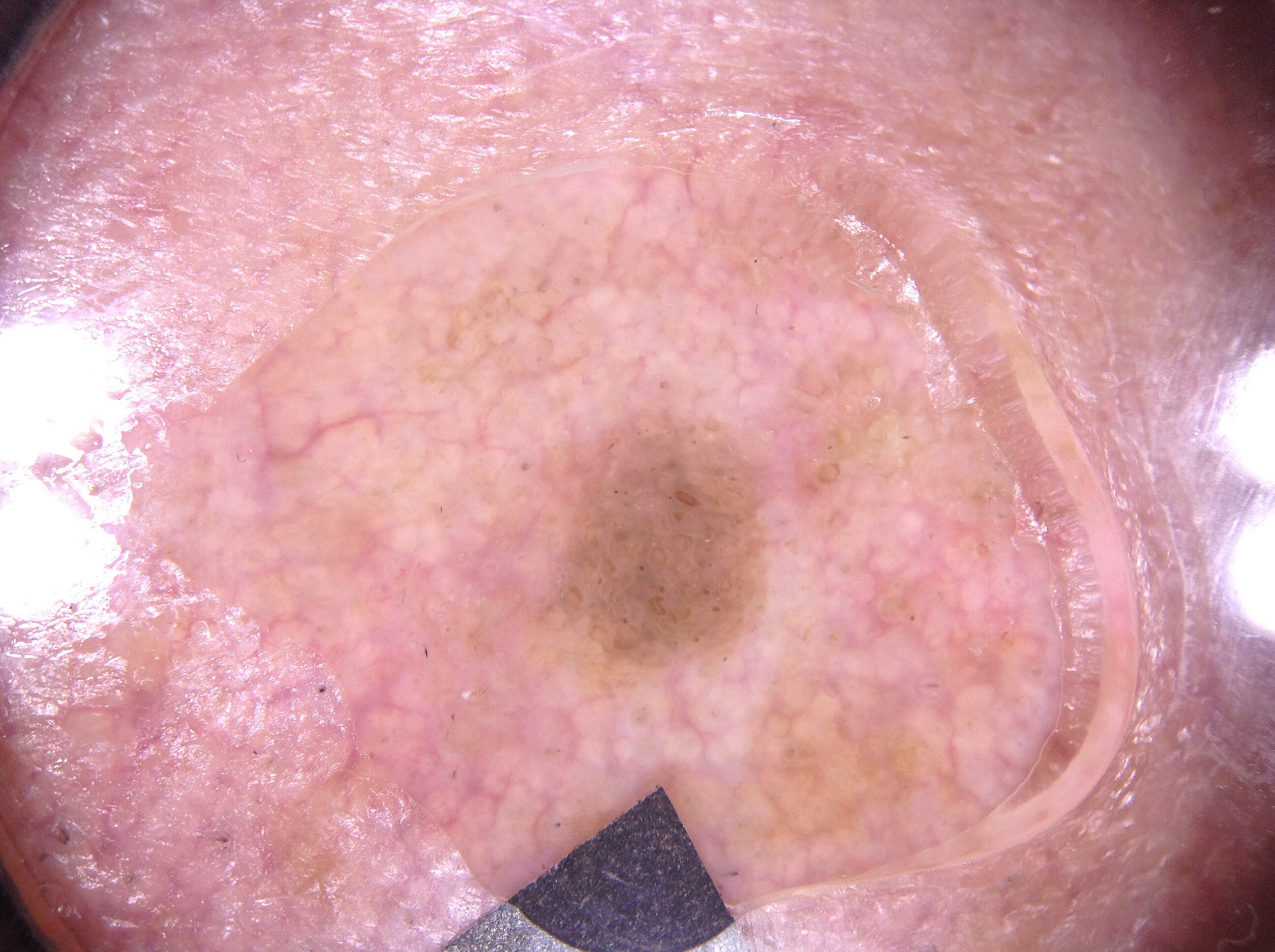Q: Who is the patient?
A: male, approximately 60 years of age
Q: What is the imaging modality?
A: dermatoscopic image of a skin lesion
Q: How large is the lesion within the image?
A: small
Q: What does dermoscopy show?
A: milia-like cysts
Q: Where is the lesion in the image?
A: box(578, 432, 757, 655)
Q: What is this lesion?
A: a seborrheic keratosis